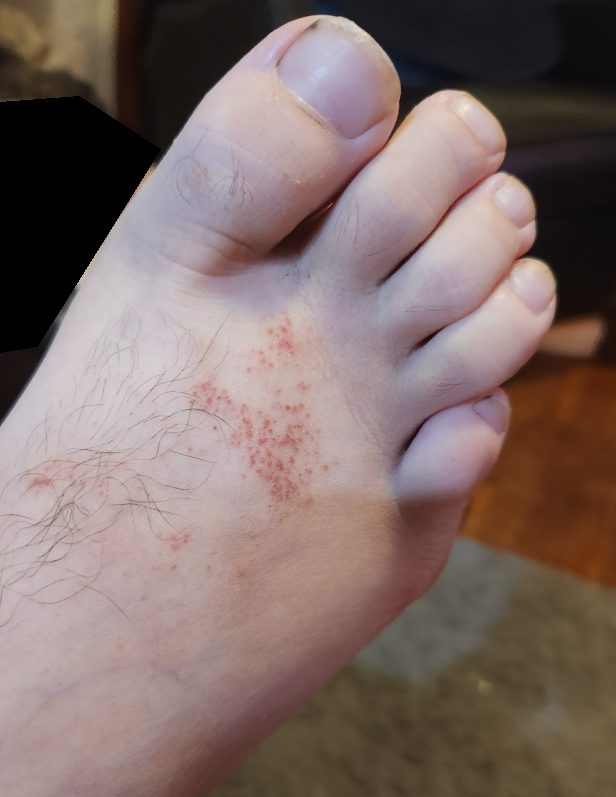The photograph is a close-up of the affected area. The reviewing clinician's impression was: the leading consideration is Pigmented purpuric eruption; an alternative is Leukocytoclastic Vasculitis.